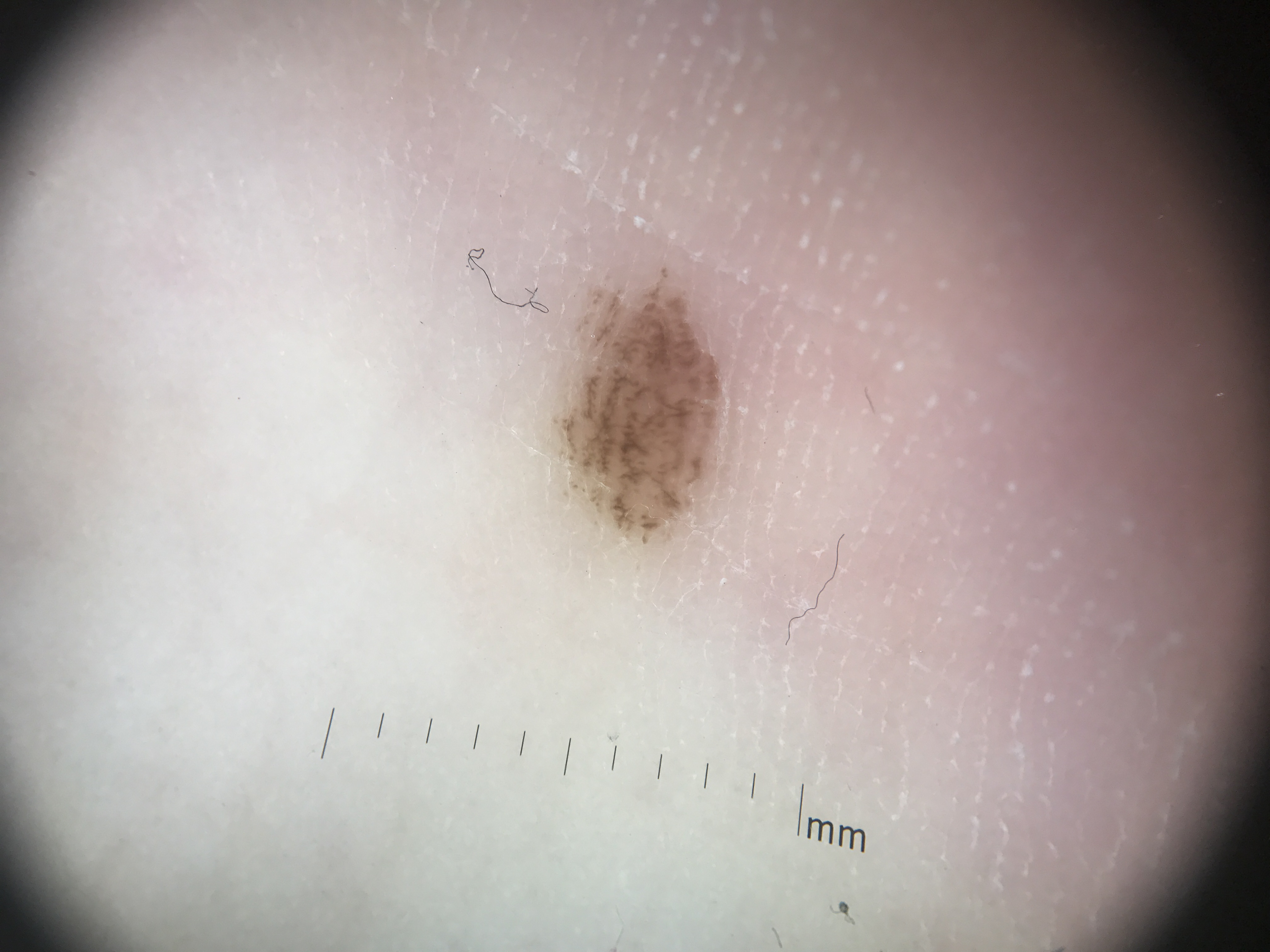Labeled as an acral dysplastic junctional nevus.